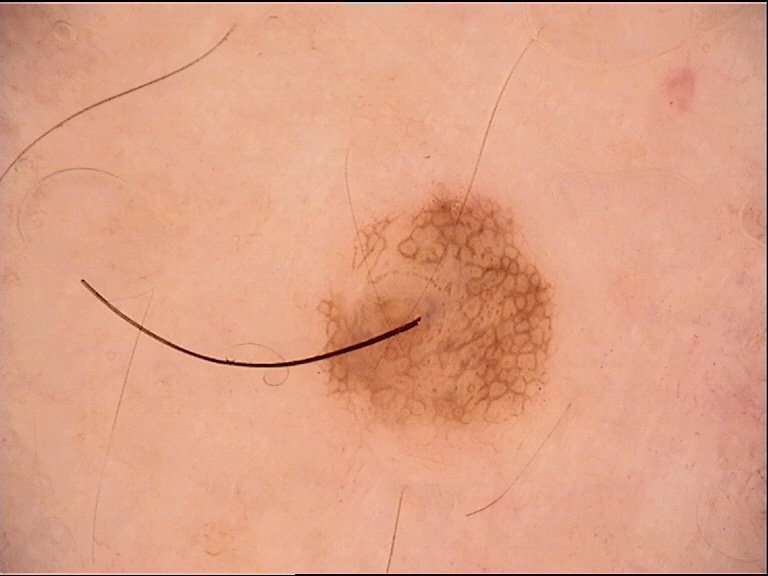label=compound nevus (expert consensus).